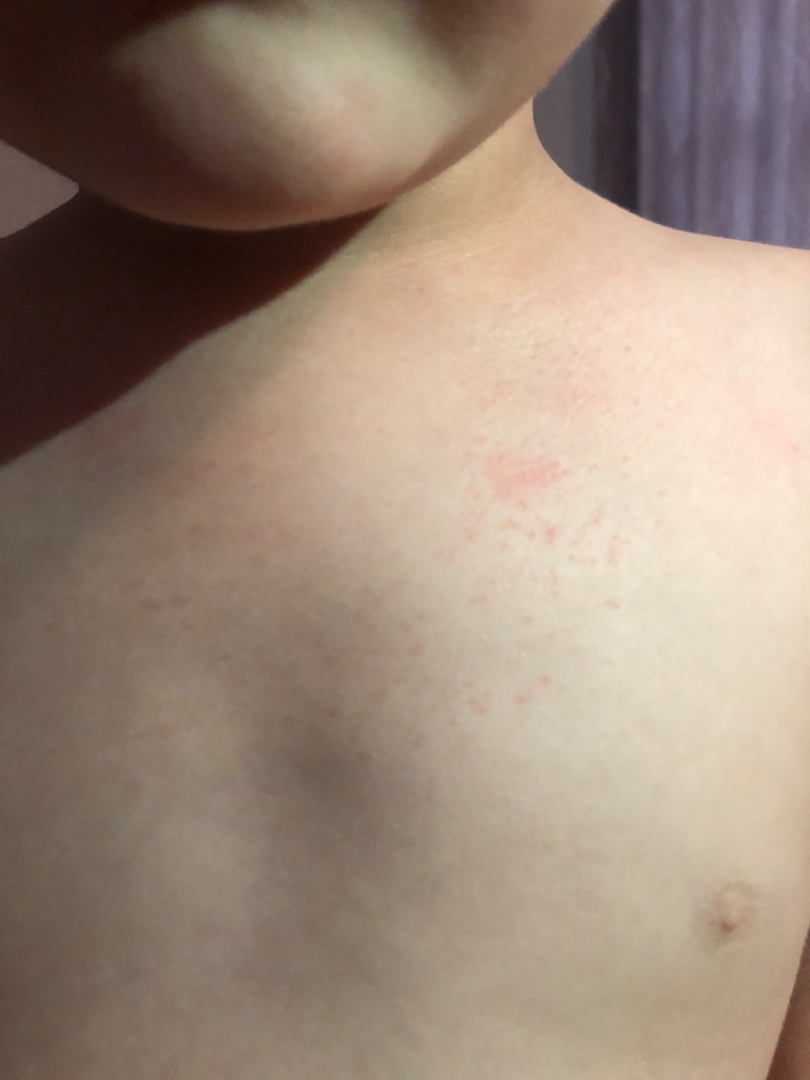The front of the torso and back of the torso are involved.
The photo was captured at an angle.
On dermatologist assessment of the image, the leading consideration is Eczema; the differential also includes Viral Exanthem; also consider Drug Rash.